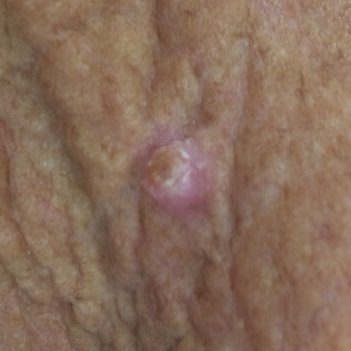imaging: clinical photo | exposure history: prior malignancy (patient or family) | skin type: III | patient: female, in their mid-60s | location: the neck | size: approx. 5 × 4 mm | patient-reported symptoms: itching, elevation / no bleeding, no pain | diagnostic label: squamous cell carcinoma (biopsy-proven).